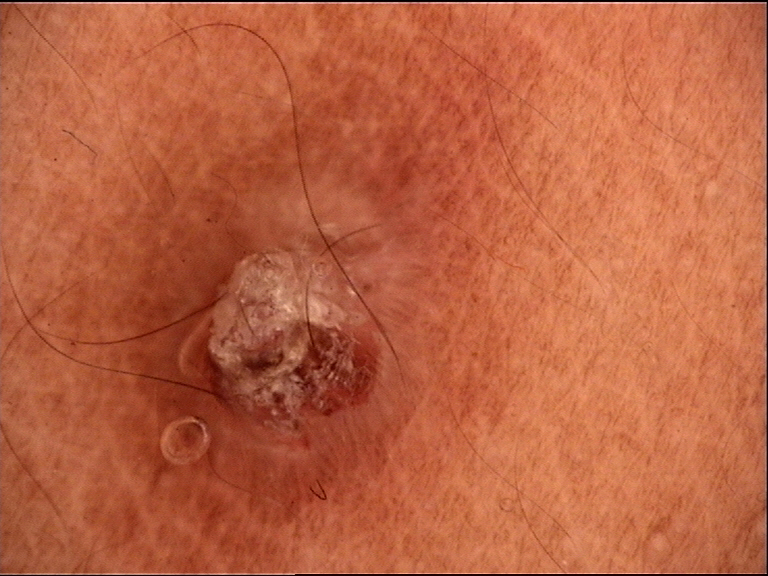{"diagnosis": {"name": "cutaneous horn", "code": "ch", "malignancy": "malignant", "super_class": "non-melanocytic", "confirmation": "histopathology"}}